A dermatoscopic image of a skin lesion.
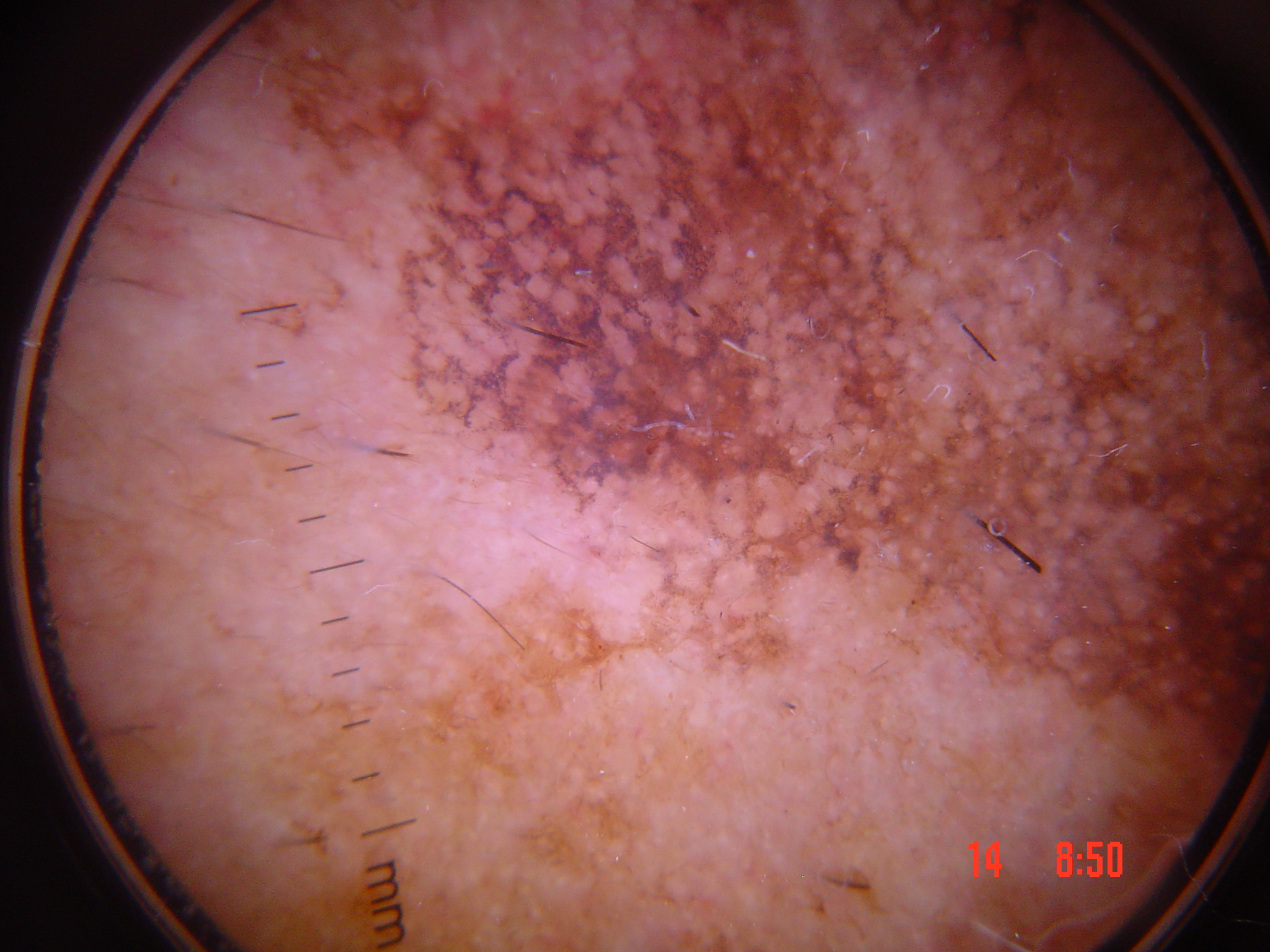Diagnosed as a keratinocytic lesion — an actinic keratosis.